The patient is a female aged 13 to 17; a skin lesion imaged with a dermatoscope: 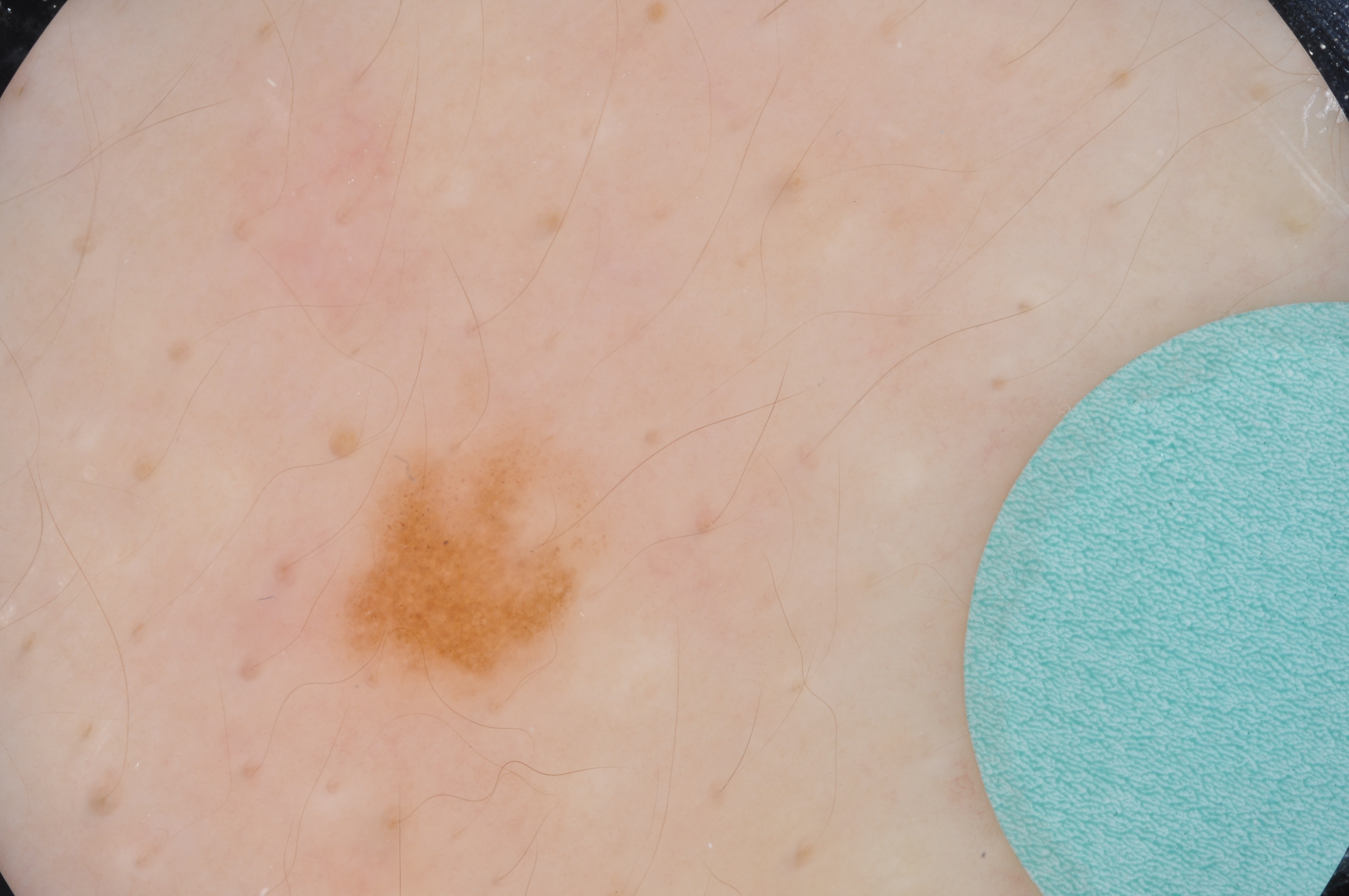On dermoscopy, the lesion shows pigment network. The lesion is located at 328, 411, 617, 721. Clinically diagnosed as a melanocytic nevus, a benign lesion.